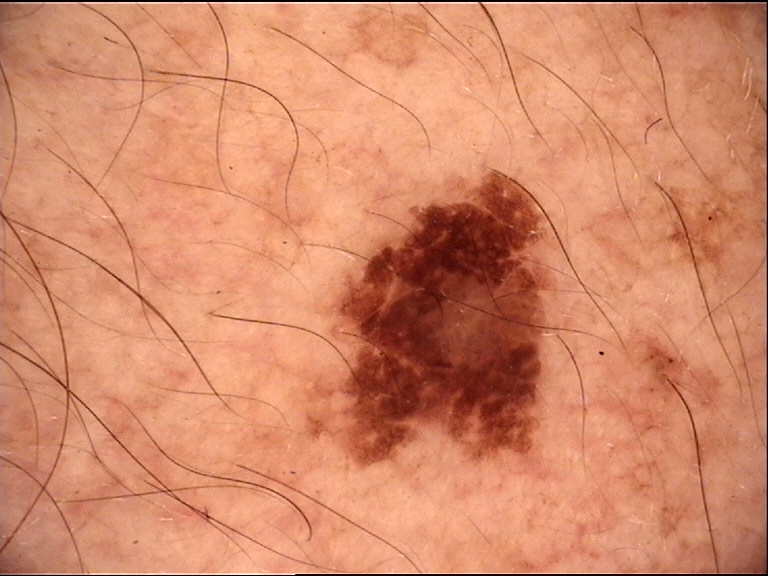{"diagnosis": {"name": "lentigo maligna", "code": "lm", "malignancy": "malignant", "super_class": "melanocytic", "confirmation": "histopathology"}}